An image taken at an angle.
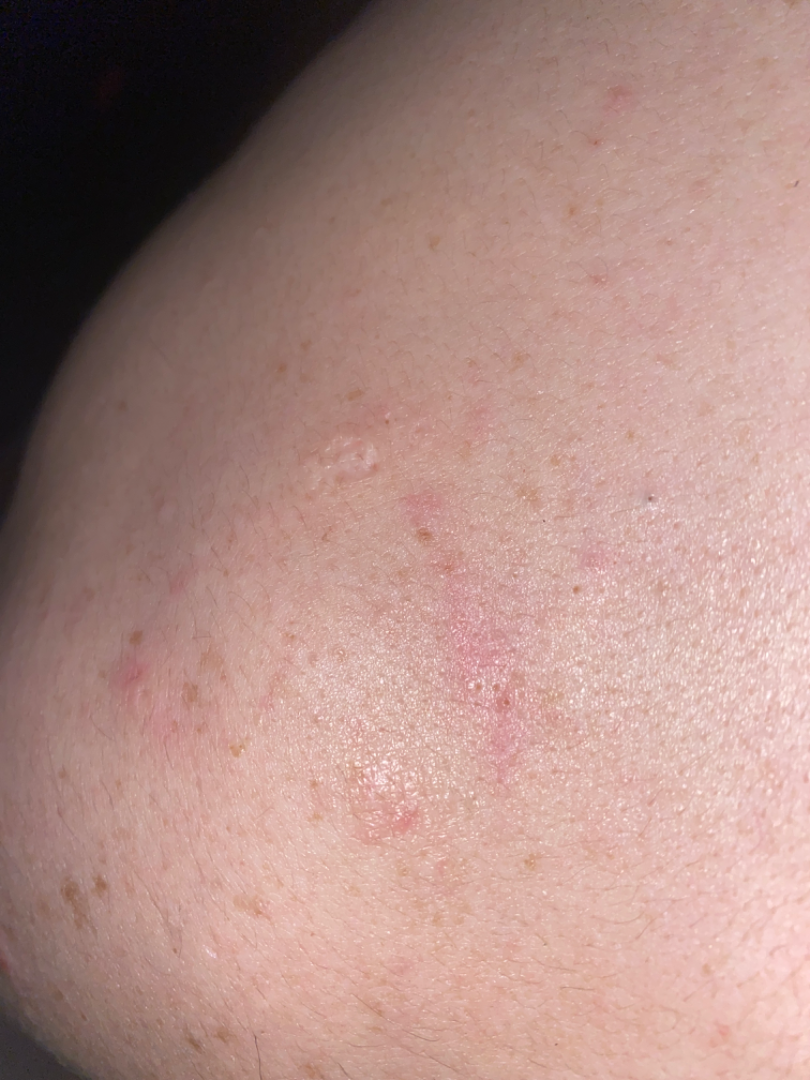differential:
  leading:
    - Eczema